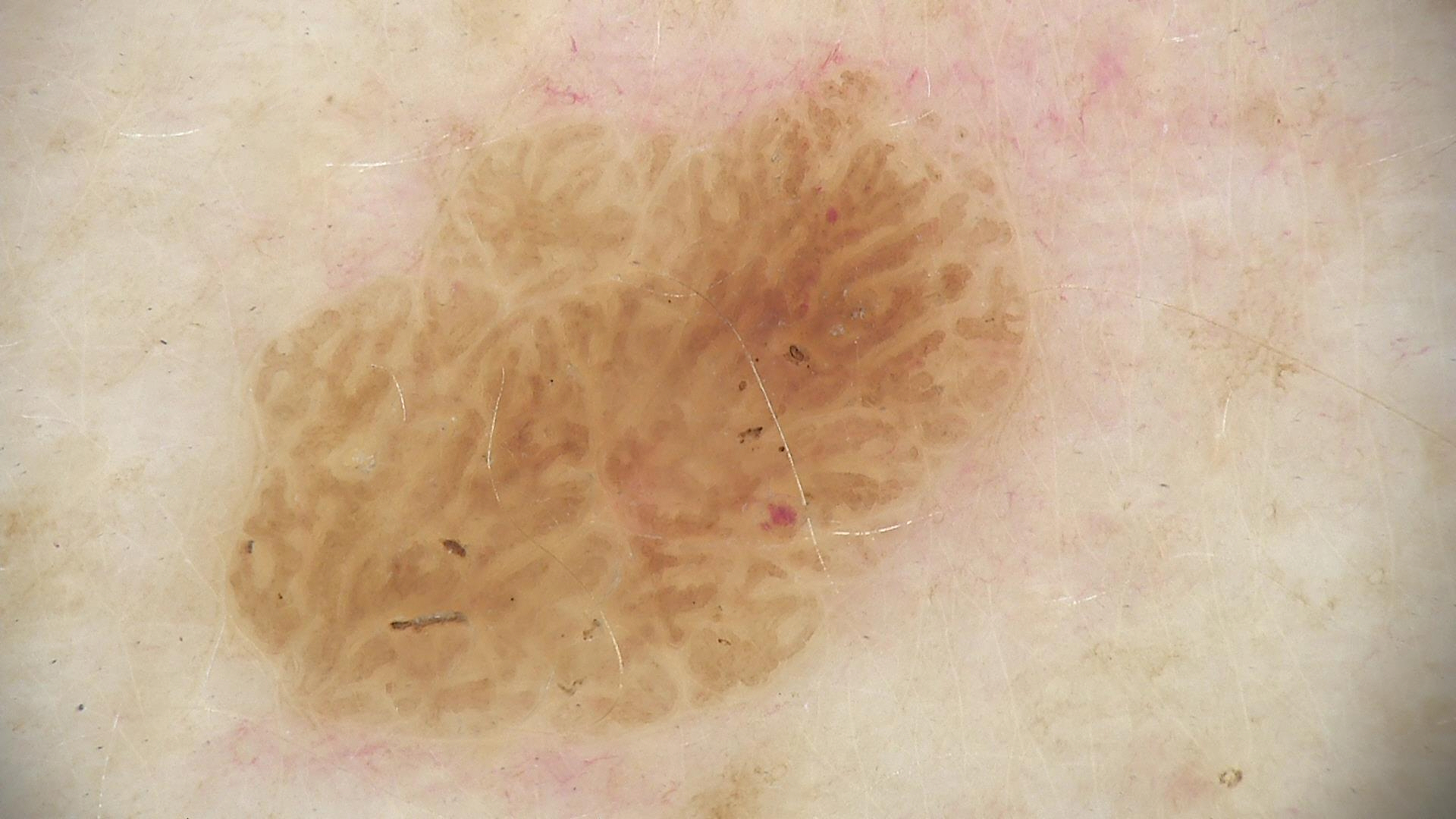Dermoscopy of a skin lesion. The morphology is that of a keratinocytic lesion. Diagnosed as a benign lesion — a seborrheic keratosis.